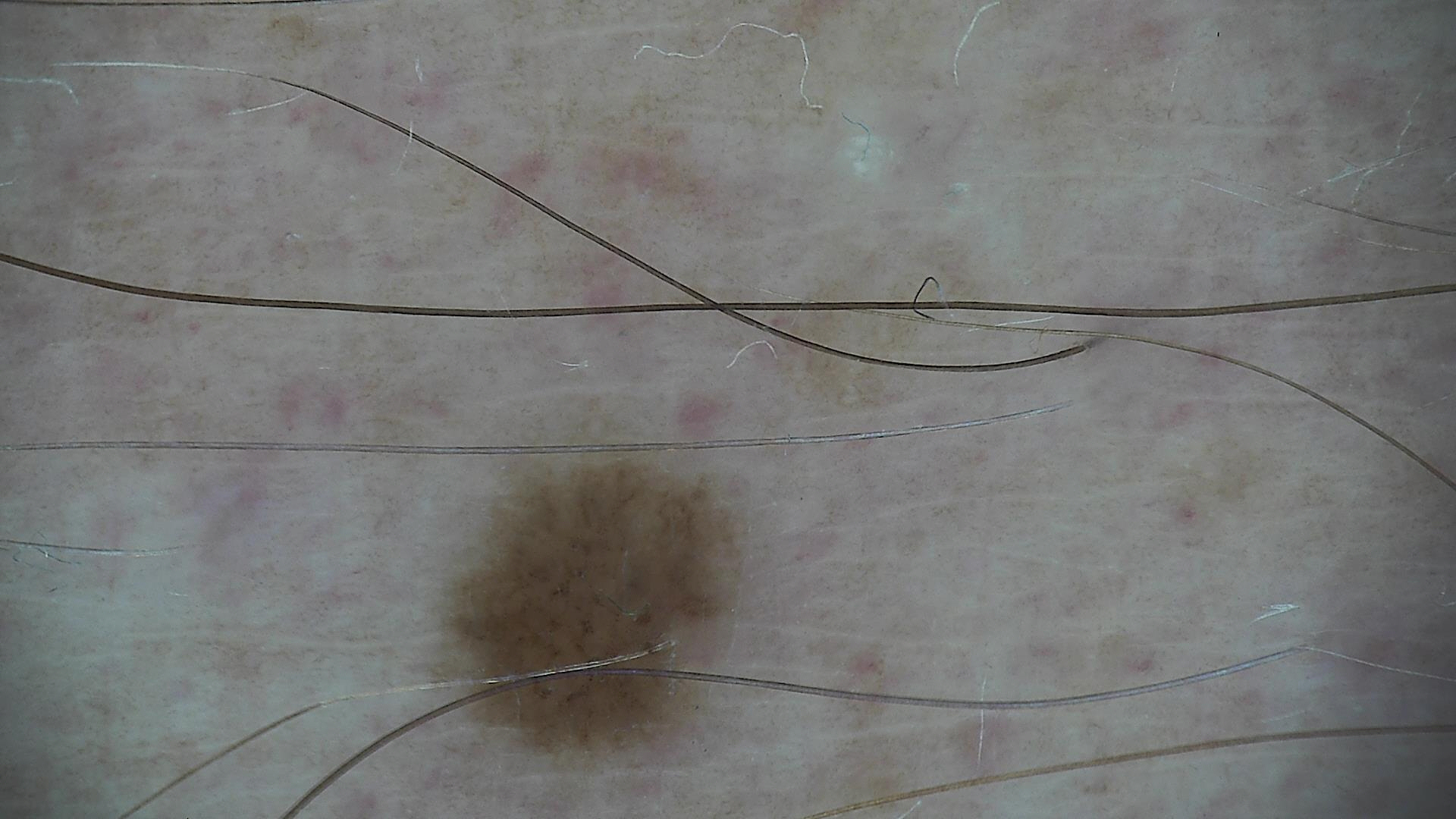modality: dermatoscopy
lesion type: banal
assessment: junctional nevus (expert consensus)